An image taken at an angle. The palm, head or neck, front of the torso and arm are involved. Self-categorized by the patient as a rash. Female patient, age 60–69. The lesion is associated with itching. No relevant systemic symptoms. Texture is reported as raised or bumpy. The condition has been present for three to twelve months:
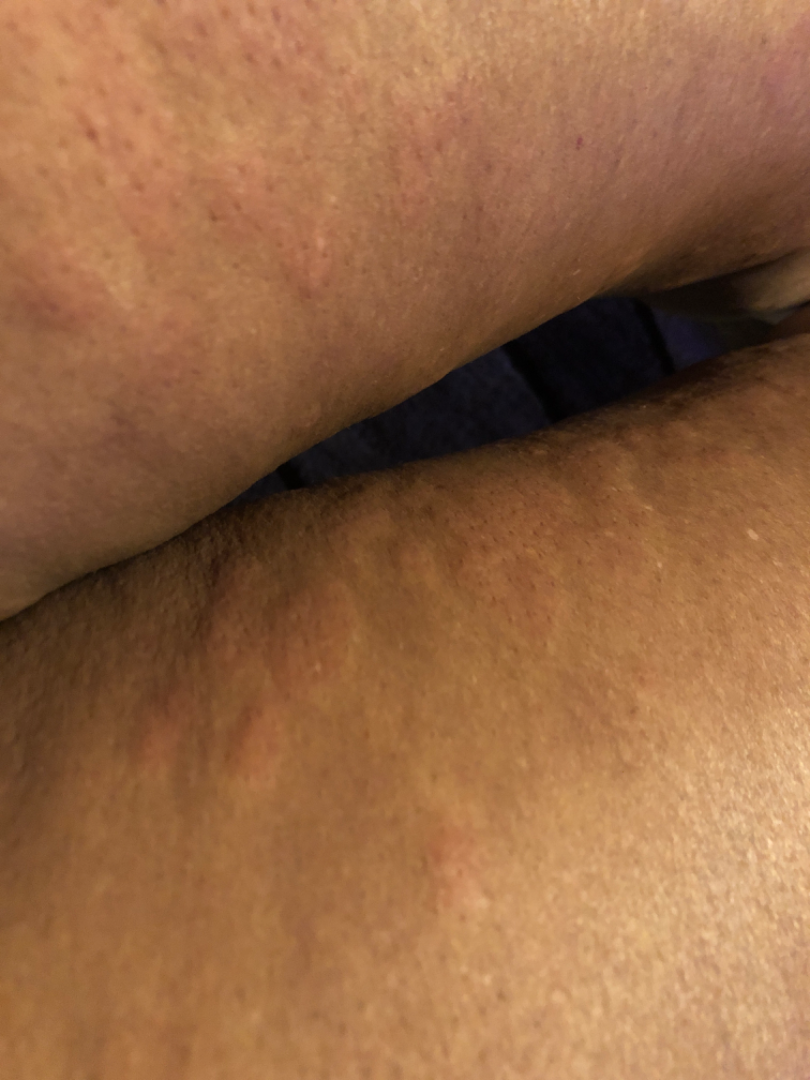| feature | finding |
|---|---|
| dermatologist impression | Urticaria (weight 1.00) |